An image taken at a distance, the affected area is the head or neck — 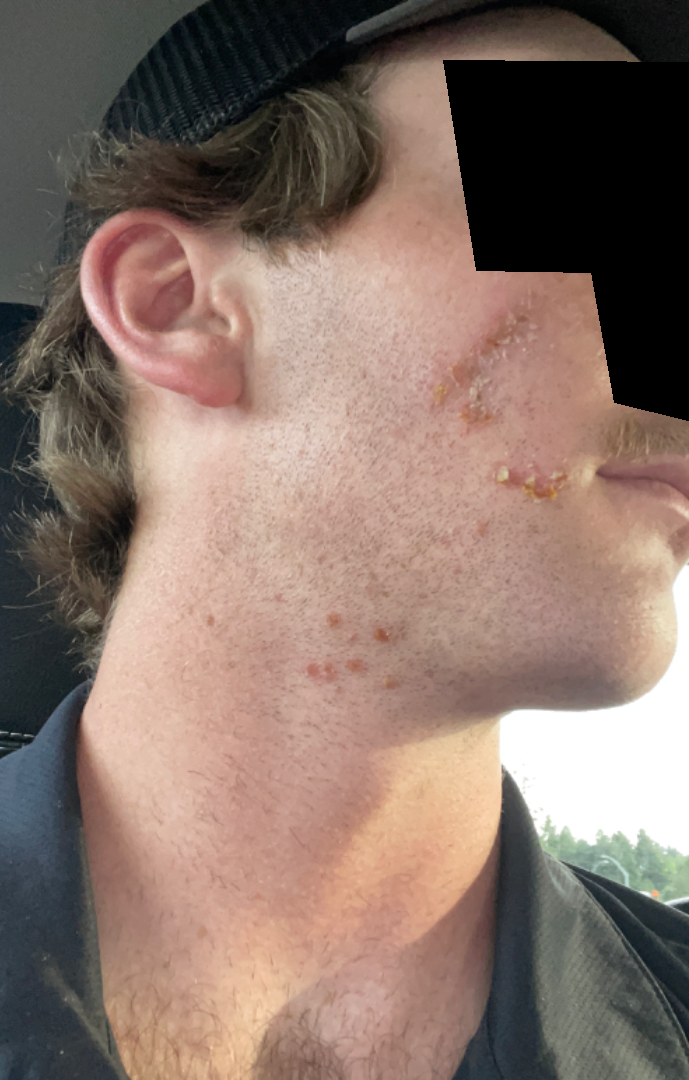* onset · one to four weeks
* diagnostic considerations · most likely Impetigo; possibly Herpes Simplex; also on the differential is Irritant Contact Dermatitis